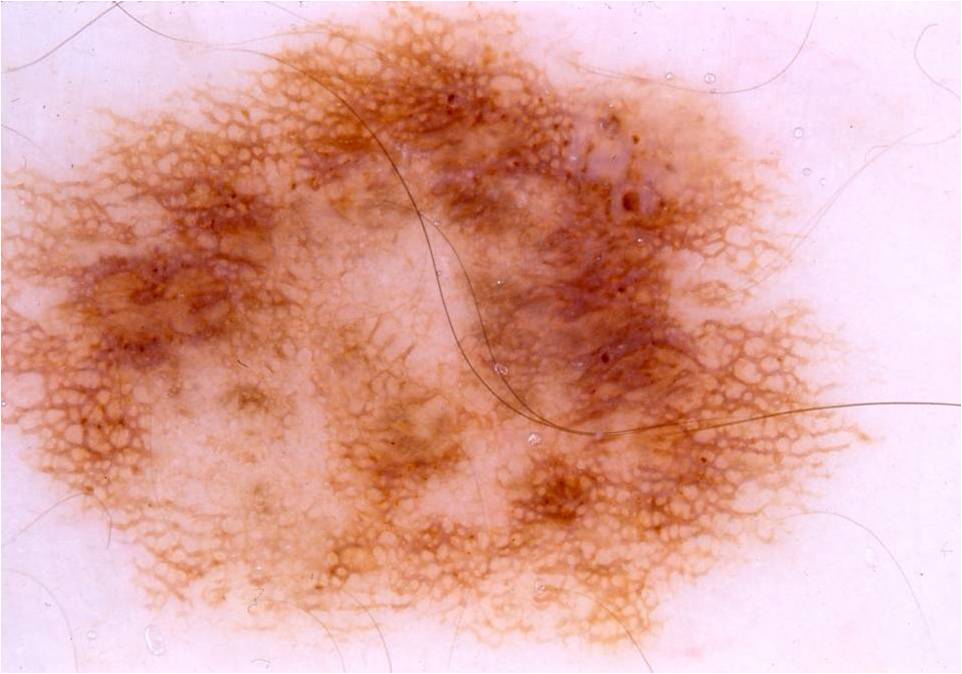Notes:
- image · dermoscopy of a skin lesion
- subject · male, aged around 45
- dermoscopic pattern · globules and pigment network; absent: streaks, negative network, and milia-like cysts
- field coverage · spans the dermoscopic field
- impression · a melanocytic nevus